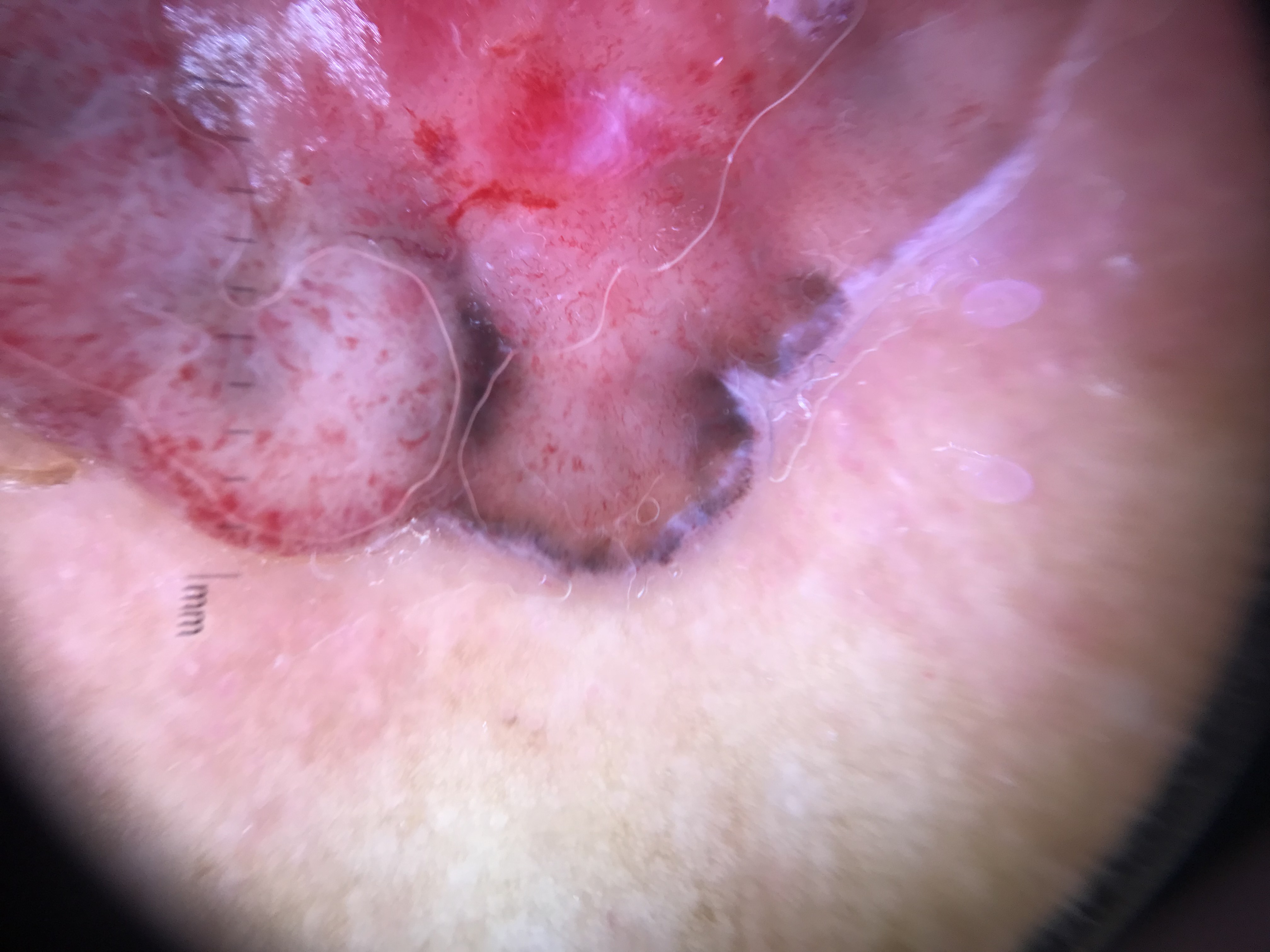Findings: A skin lesion imaged with a dermatoscope. Conclusion: The biopsy diagnosis was a keratinocytic lesion — a basal cell carcinoma.